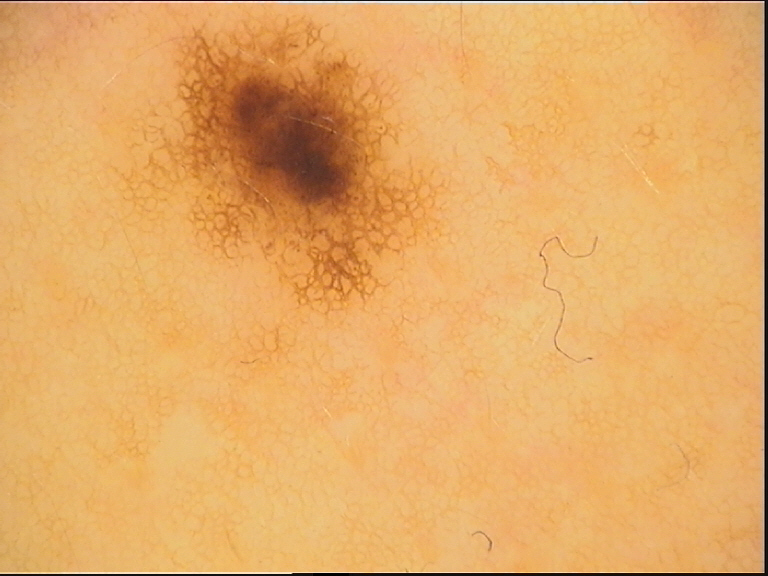A dermoscopic image of a skin lesion.
Consistent with a dysplastic junctional nevus.